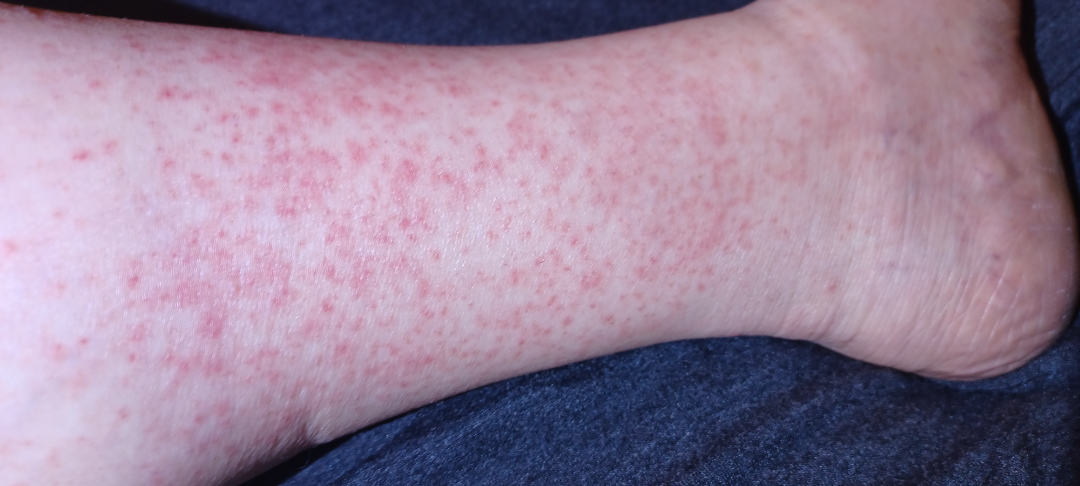The condition has been present for about one day.
This is a close-up image.
The lesion is described as flat.
Self-categorized by the patient as a rash.
Reported lesion symptoms include burning, bothersome appearance, itching, darkening and enlargement.
Located on the top or side of the foot and leg.
The reviewing dermatologist's impression was: Pigmented purpuric eruption and Leukocytoclastic Vasculitis were each considered, in no particular order.